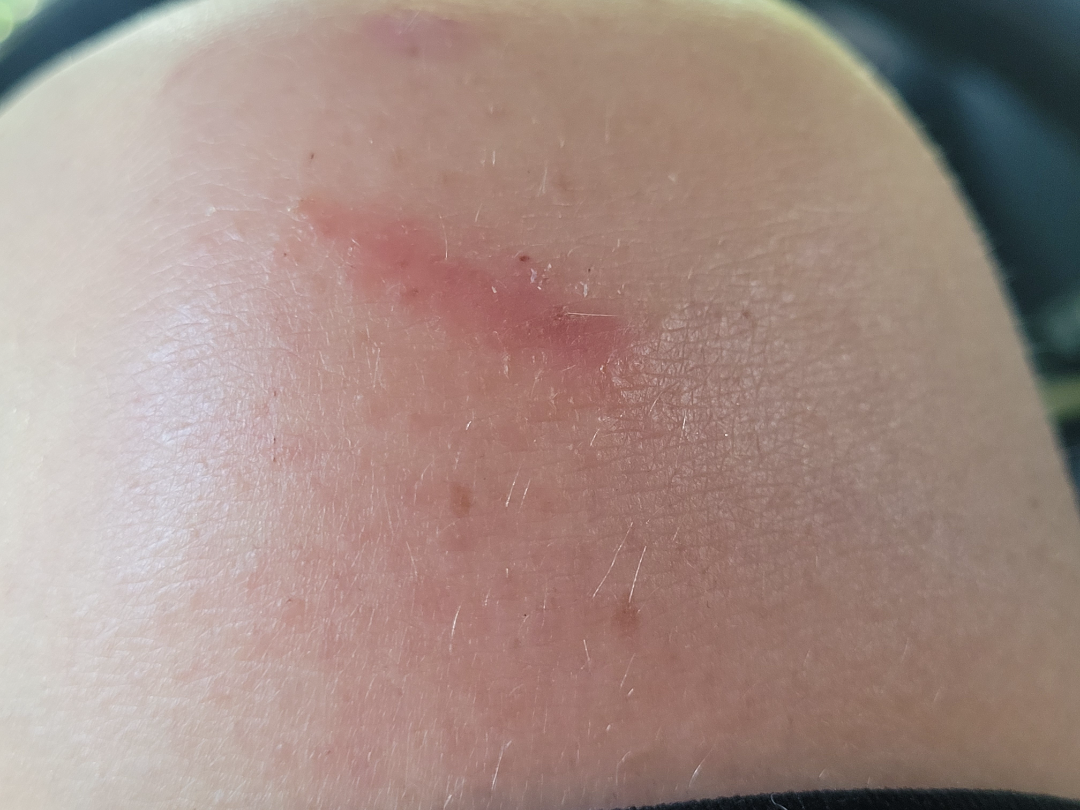Q: What was the assessment?
A: indeterminate from the photograph
Q: What is the patient's skin tone?
A: Fitzpatrick phototype II; lay reviewers estimated MST 2–3
Q: How was the photo taken?
A: close-up
Q: Where on the body?
A: leg
Q: Patient demographics?
A: female, age 18–29
Q: Any systemic symptoms?
A: none reported
Q: When did this start?
A: less than one week
Q: What symptoms does the patient report?
A: itching
Q: How does the patient describe it?
A: a rash
Q: How does the lesion feel?
A: raised or bumpy